This is a close-up image · the patient notes the lesion is rough or flaky · the patient notes the condition has been present for one to four weeks · the arm is involved.
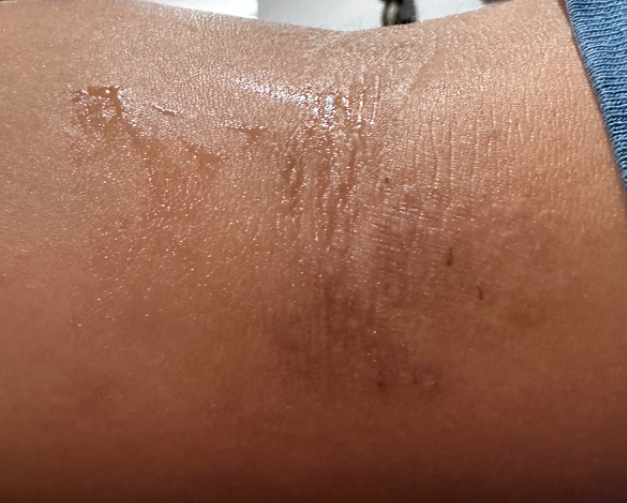Consistent with Eczema.